The patient also reports shortness of breath, joint pain and fatigue. The patient reports the condition has been present for about one day. This image was taken at an angle. No relevant lesion symptoms reported. The lesion involves the leg. Female subject, age 40–49 — 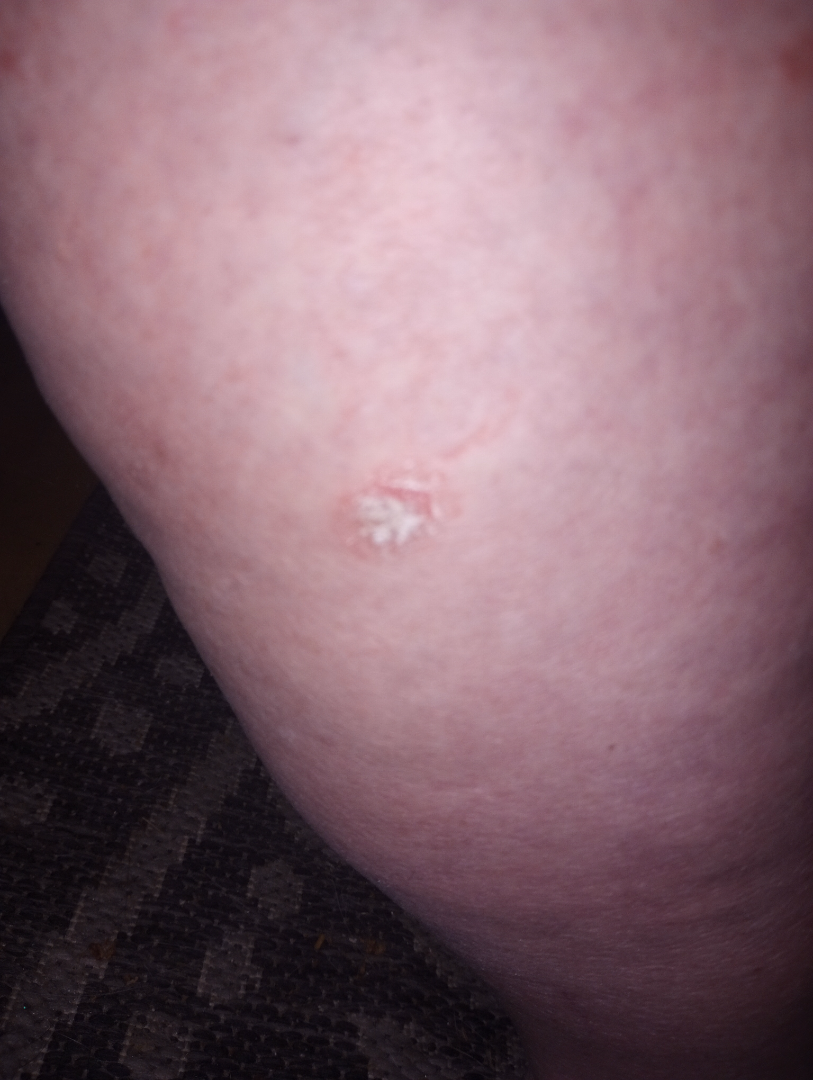Notes:
• differential diagnosis · single-reviewer assessment: the leading impression is SCC/SCCIS; possibly SK/ISK